A dermoscopic image of a skin lesion · a male subject aged 78-82.
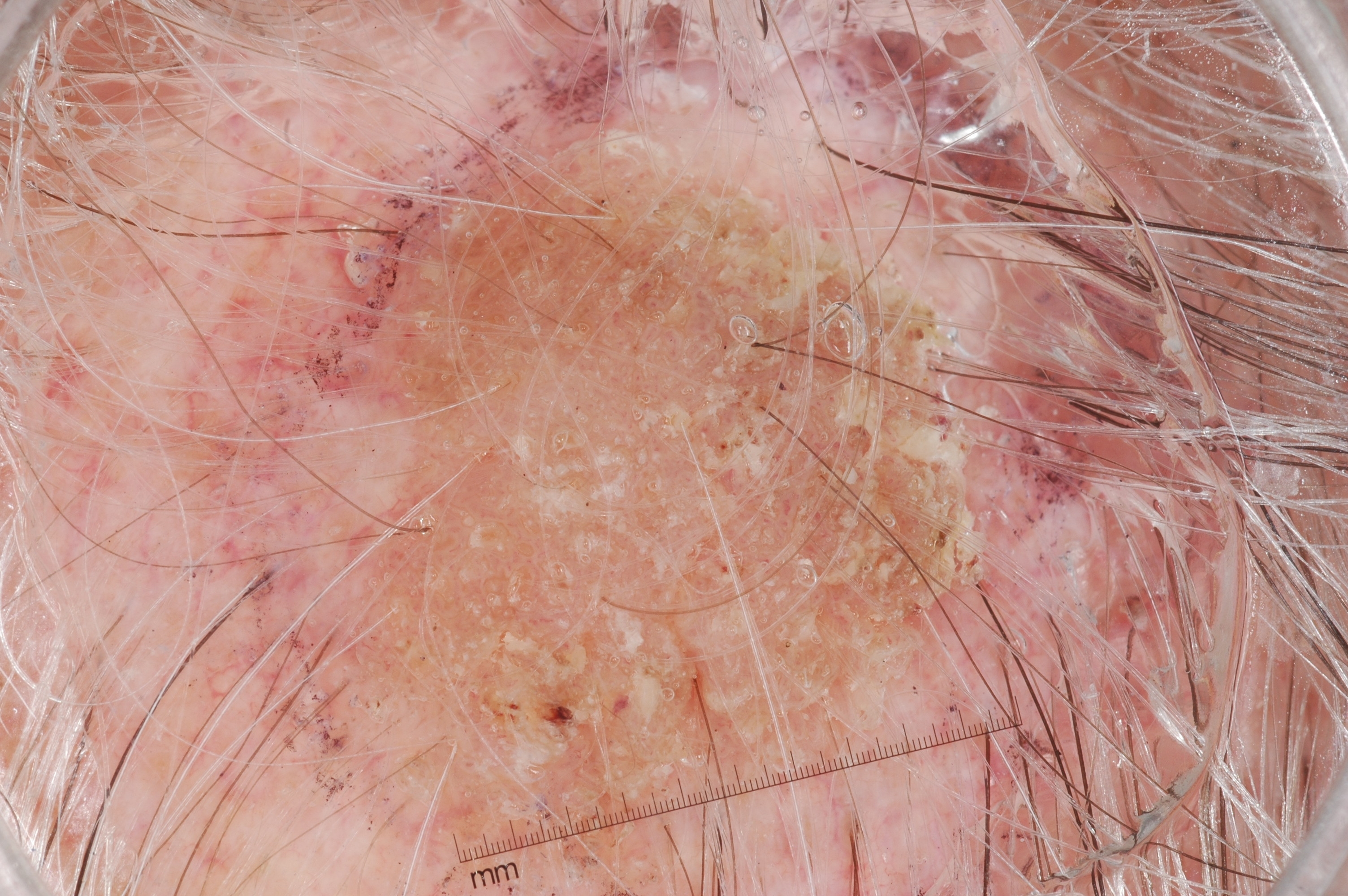The lesion takes up a large portion of the image.
The lesion occupies the region left=225, top=59, right=1033, bottom=885.
Dermoscopy demonstrates no milia-like cysts, negative network, pigment network, or streaks.
The clinical diagnosis was a seborrheic keratosis, a keratinocytic lesion.